A dermatoscopic image of a skin lesion: 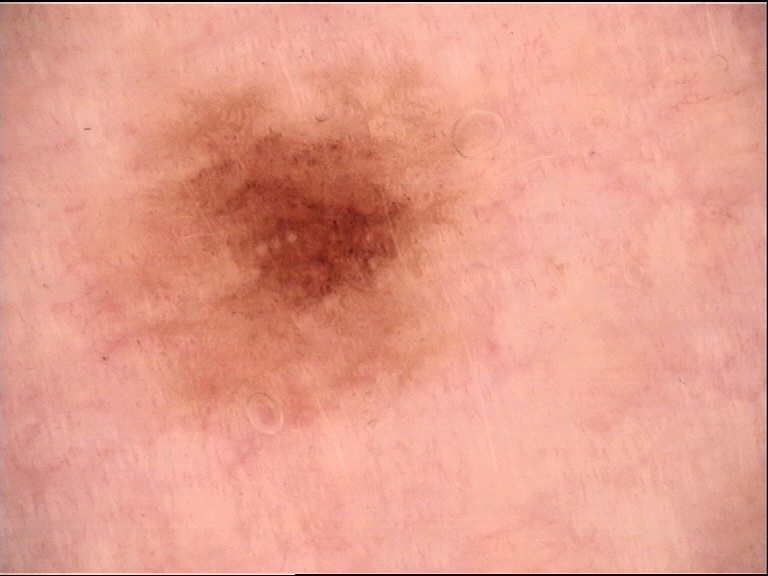diagnosis — dysplastic junctional nevus (expert consensus).